A dermoscopic image of a skin lesion.
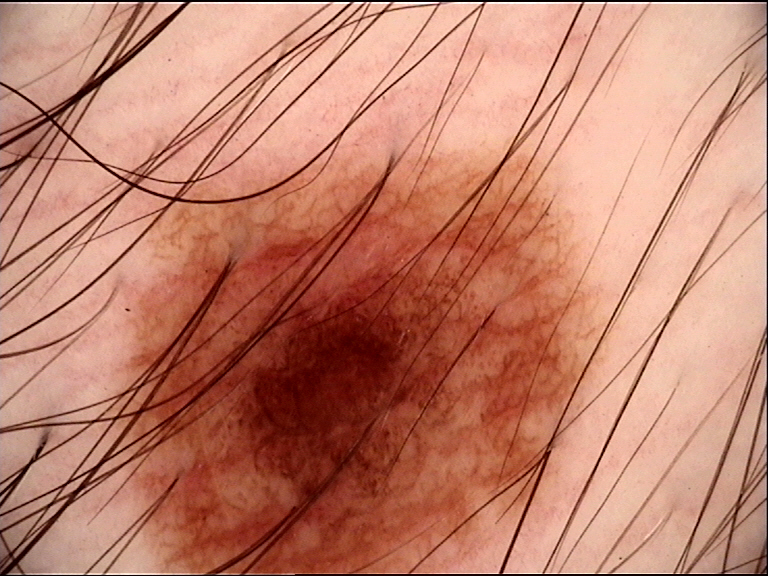diagnostic label — dysplastic junctional nevus (expert consensus).